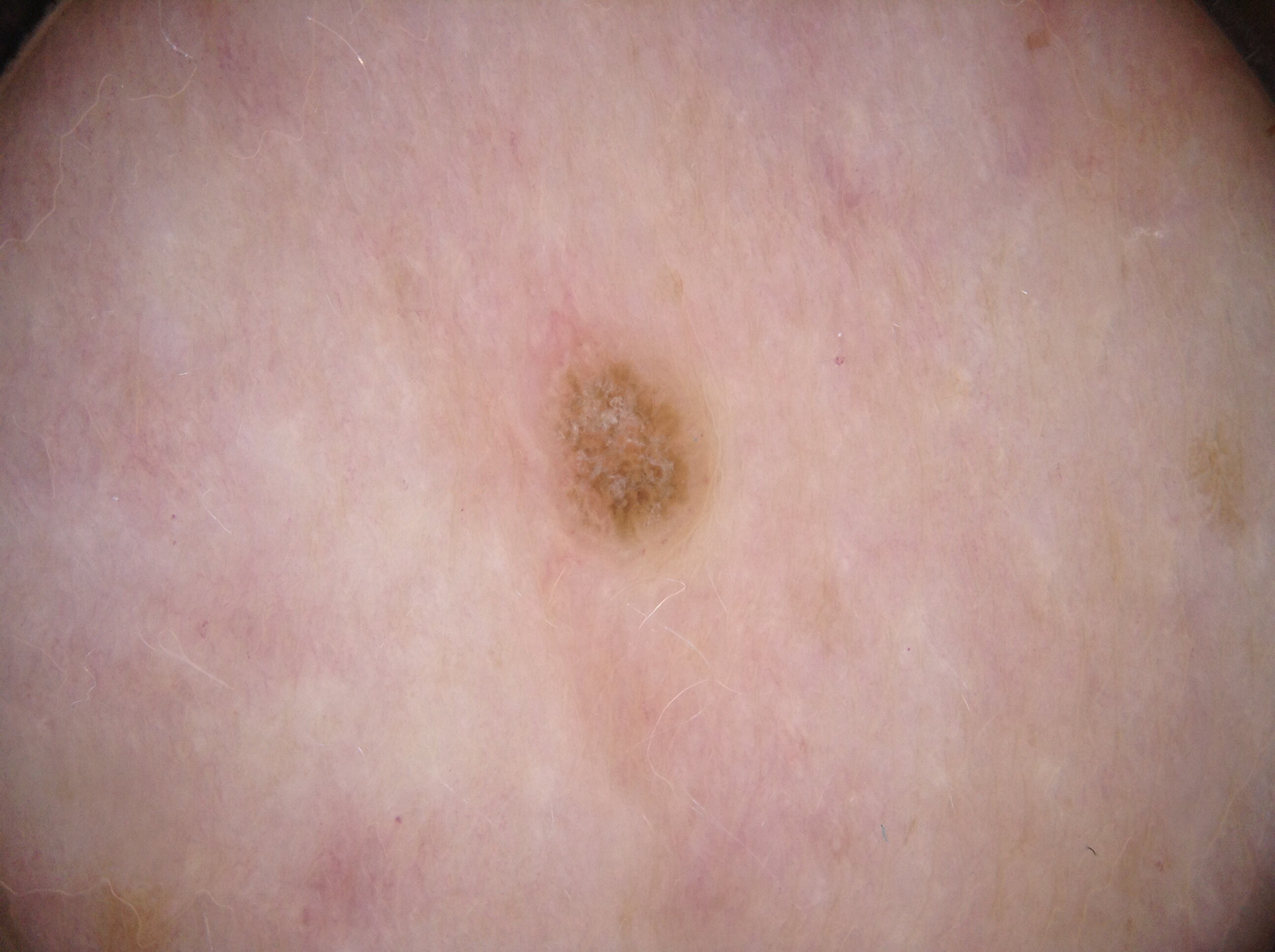Q: What is the imaging modality?
A: dermoscopic image
Q: Patient demographics?
A: female, about 70 years old
Q: Lesion extent?
A: ~2% of the field
Q: Where is the lesion located?
A: bbox=[559, 342, 707, 543]
Q: Which assessed dermoscopic features were absent?
A: streaks, milia-like cysts, pigment network, and negative network
Q: What is this lesion?
A: a seborrheic keratosis